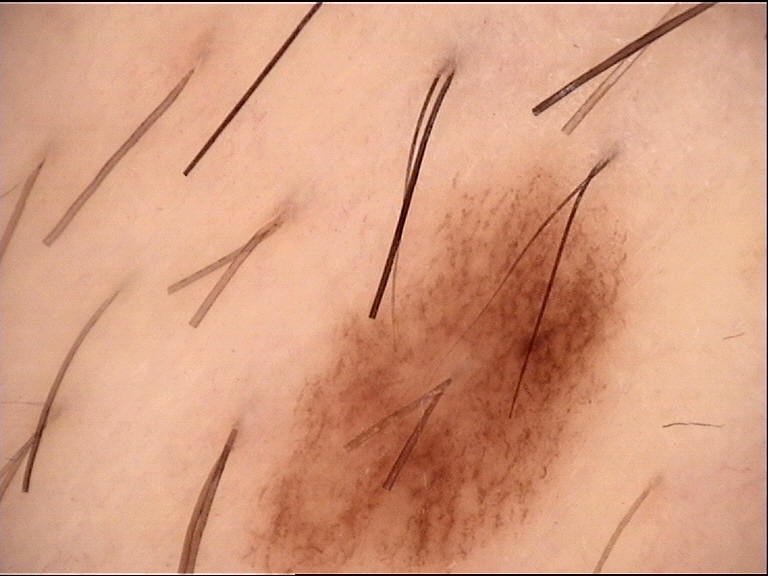Findings:
- image — dermoscopy
- class — dysplastic junctional nevus (expert consensus)